A female subject 52 years old: 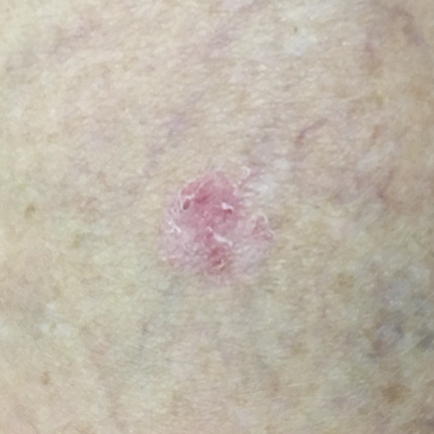location: a thigh
reported symptoms: growth, bleeding, itching
diagnostic label: basal cell carcinoma (biopsy-proven)